Per the chart, melanoma in a first-degree relative; contact-polarized dermoscopy of a skin lesion; a female patient approximately 35 years of age: 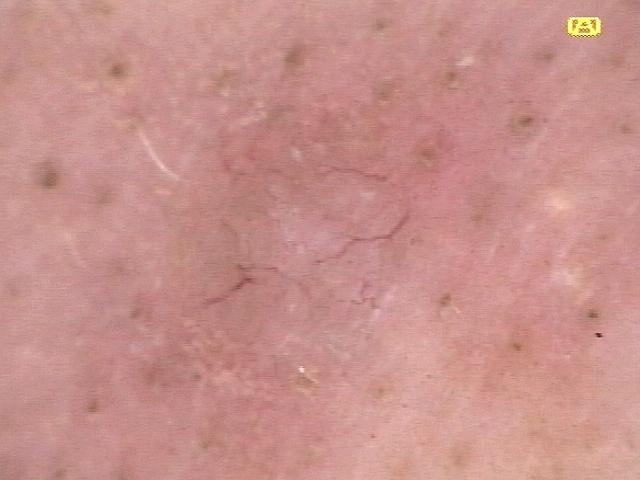<skin_lesion>
  <diagnosis>
    <name>Nevus</name>
    <malignancy>benign</malignancy>
    <confirmation>histopathology</confirmation>
    <lineage>melanocytic</lineage>
  </diagnosis>
</skin_lesion>